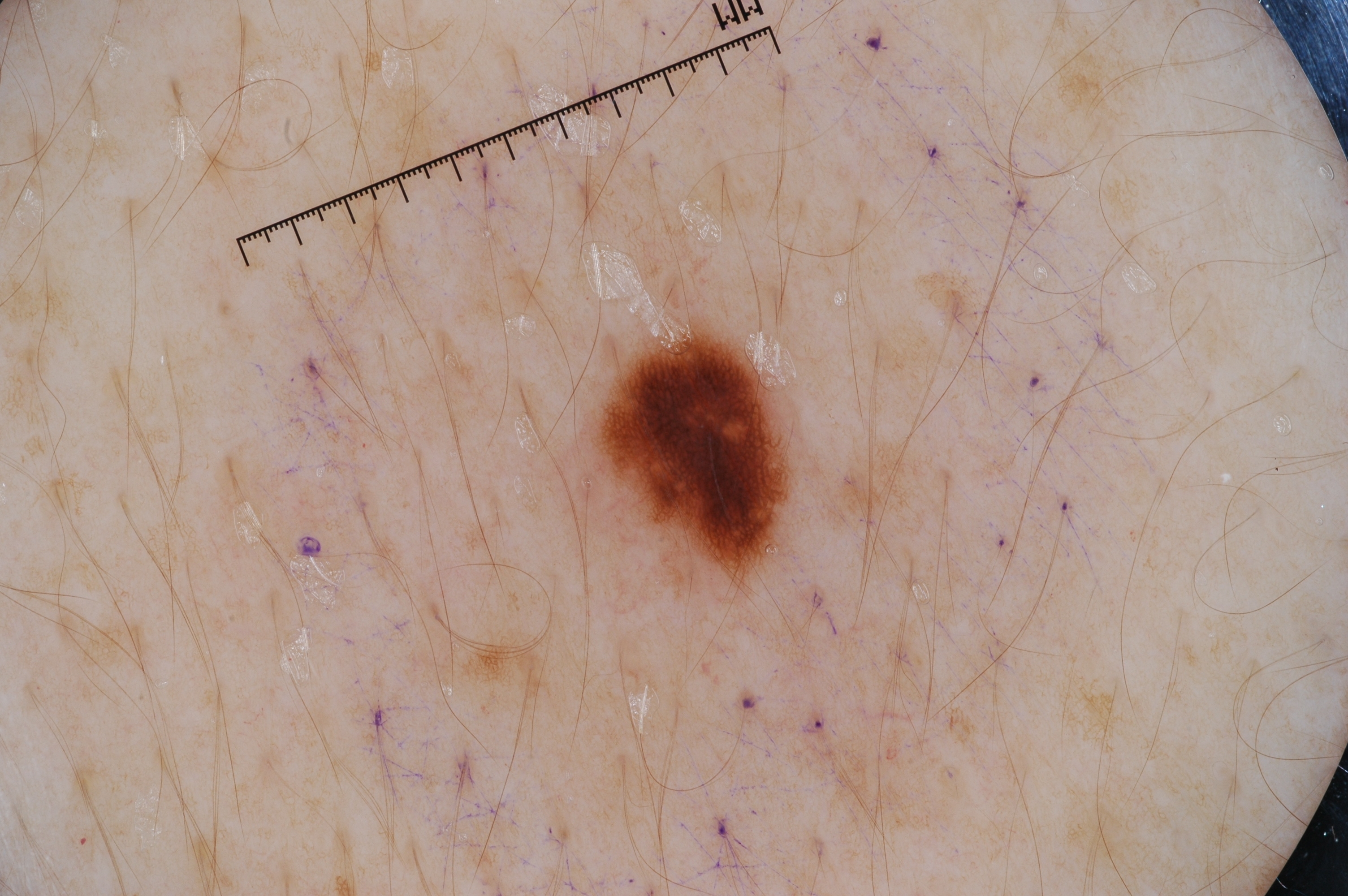Case summary:
* image type · dermoscopic image
* subject · female, aged 33-37
* lesion location · x1=590, y1=336, x2=790, y2=574
* dermoscopic features · pigment network
* impression · a melanocytic nevus